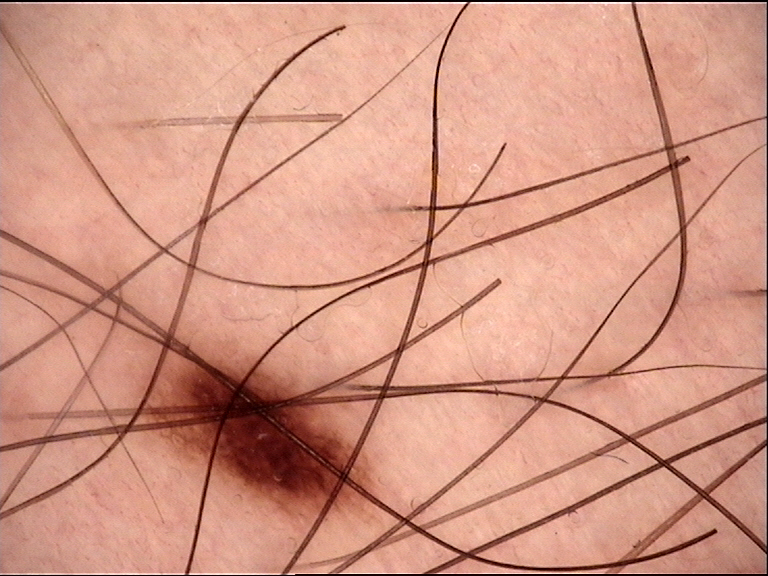A skin lesion imaged with a dermatoscope.
Classified as a benign lesion — a dysplastic junctional nevus.